A clinical photograph showing a skin lesion · a subject 73 years old.
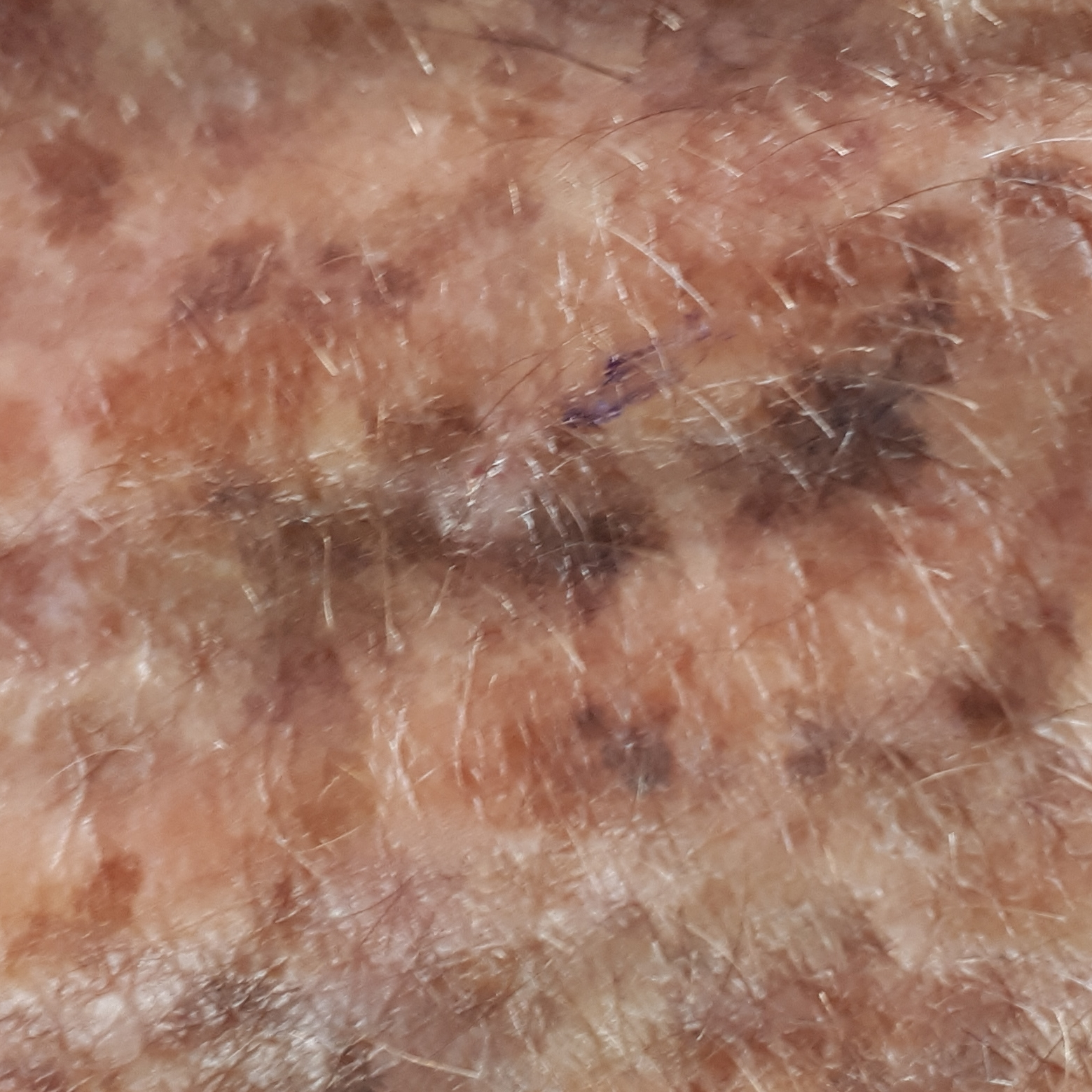Q: Where on the body is the lesion?
A: a hand
Q: Any reported symptoms?
A: elevation / no change in appearance, no itching
Q: What is the diagnosis?
A: seborrheic keratosis (clinical consensus)